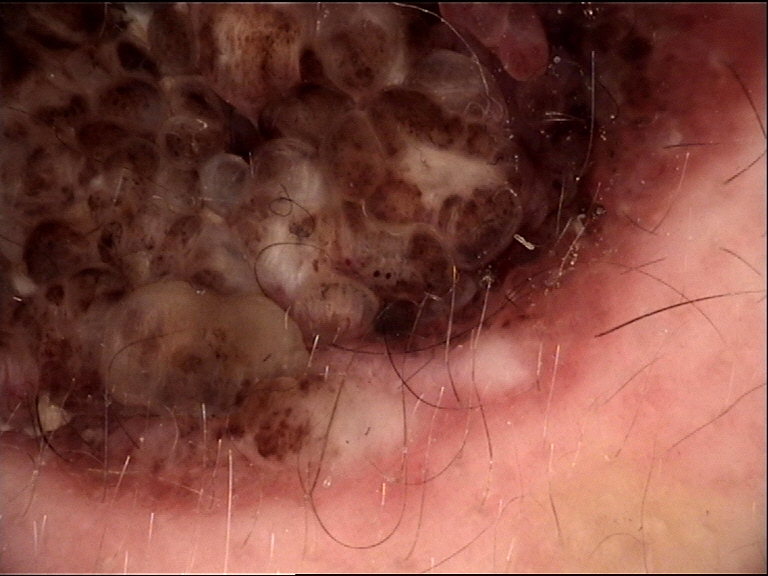A dermoscopic image of a skin lesion. Diagnosed as a banal lesion — a congenital compound nevus.